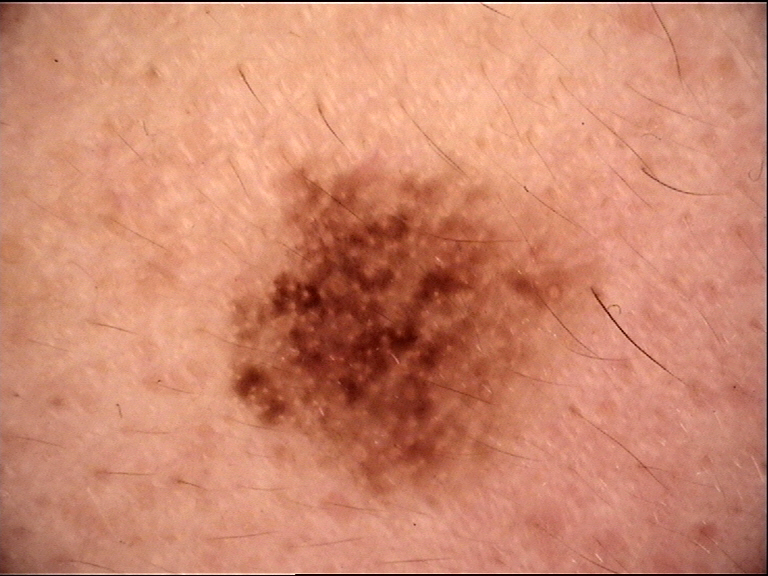The architecture is that of a banal, compound lesion. The diagnosis was a Miescher nevus.